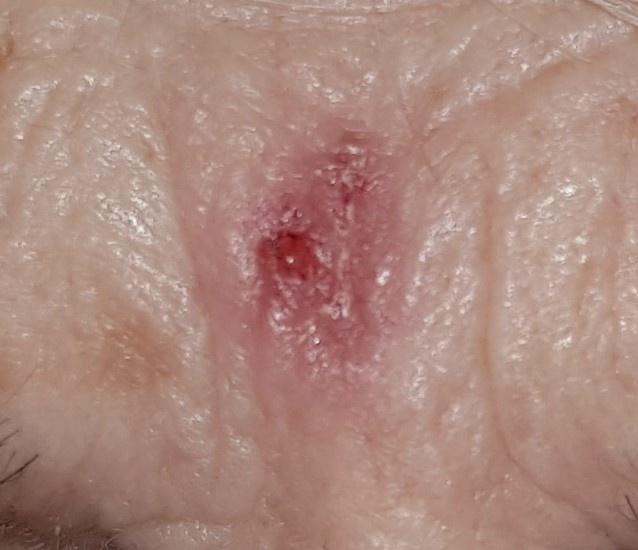Image and clinical context: The lesion is located on the head or neck. Pathology: Biopsy-confirmed as a basal cell carcinoma.